A dermoscopy image of a single skin lesion.
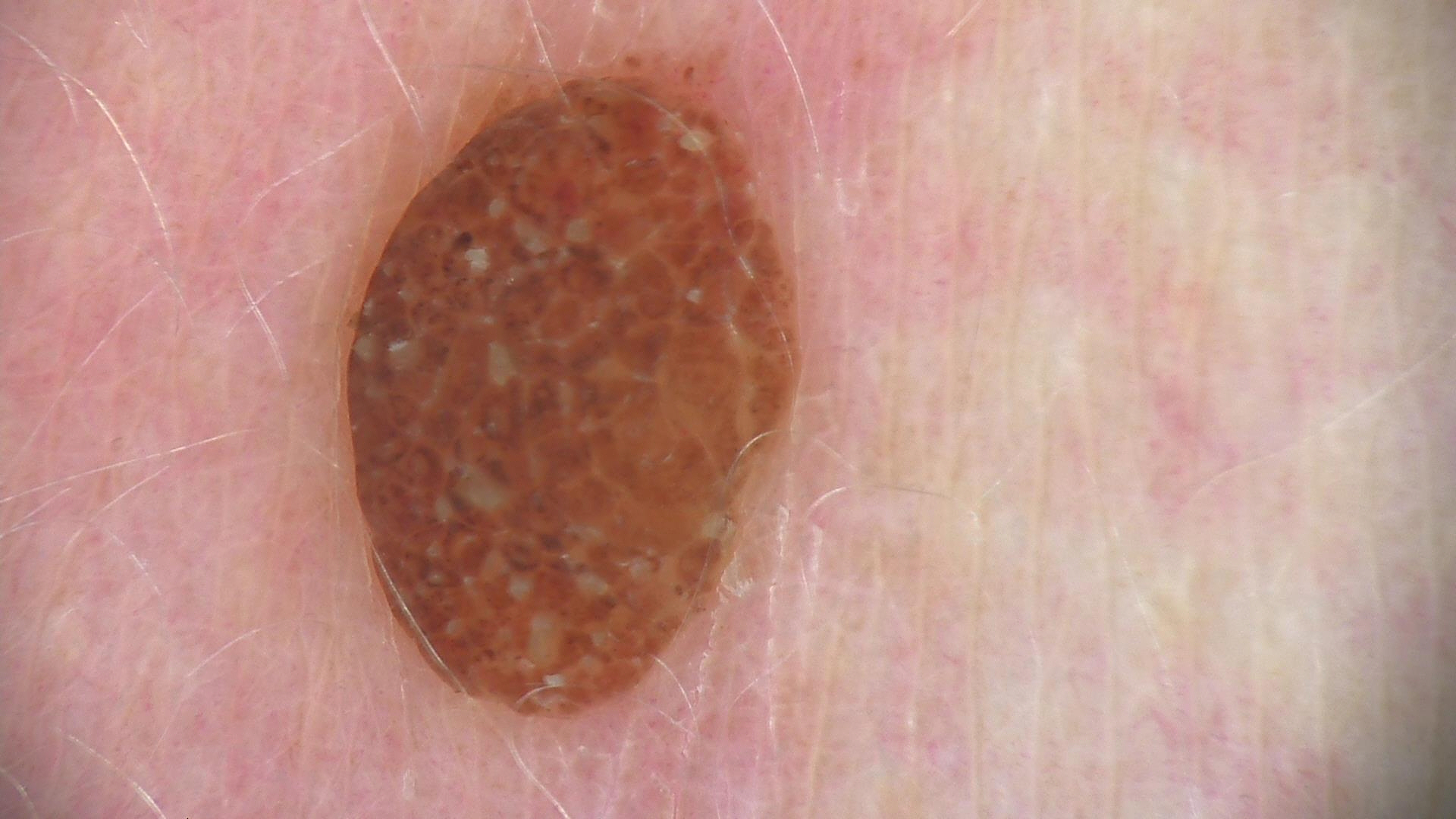The diagnostic label was a banal lesion — a dermal nevus.